Self-categorized by the patient as a rash. Close-up view:
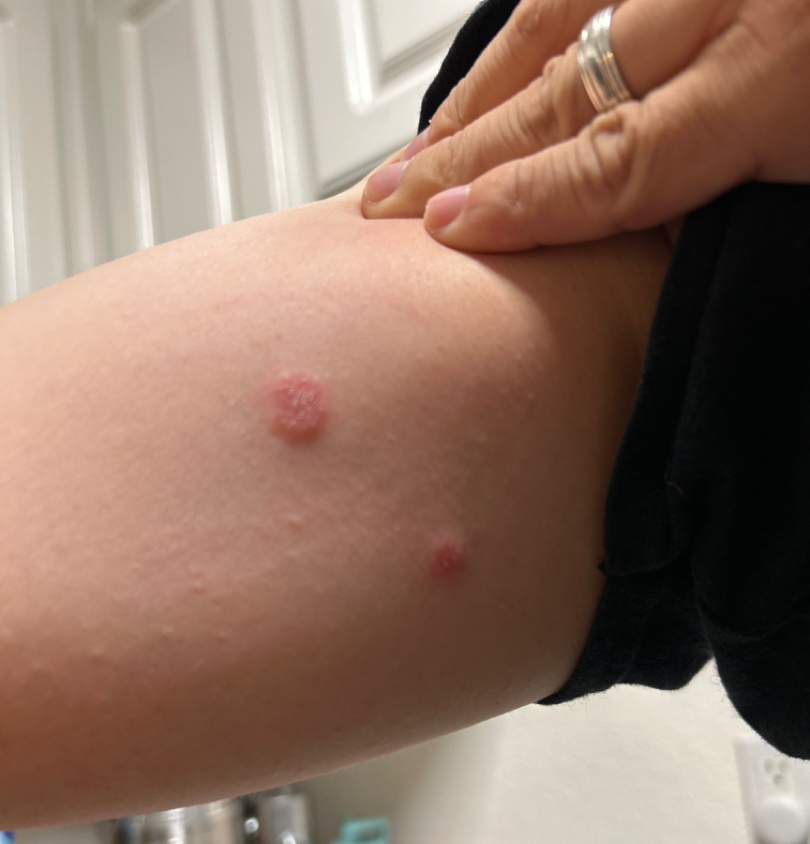Eczema (1.00).